This is a close-up image · the lesion involves the head or neck: 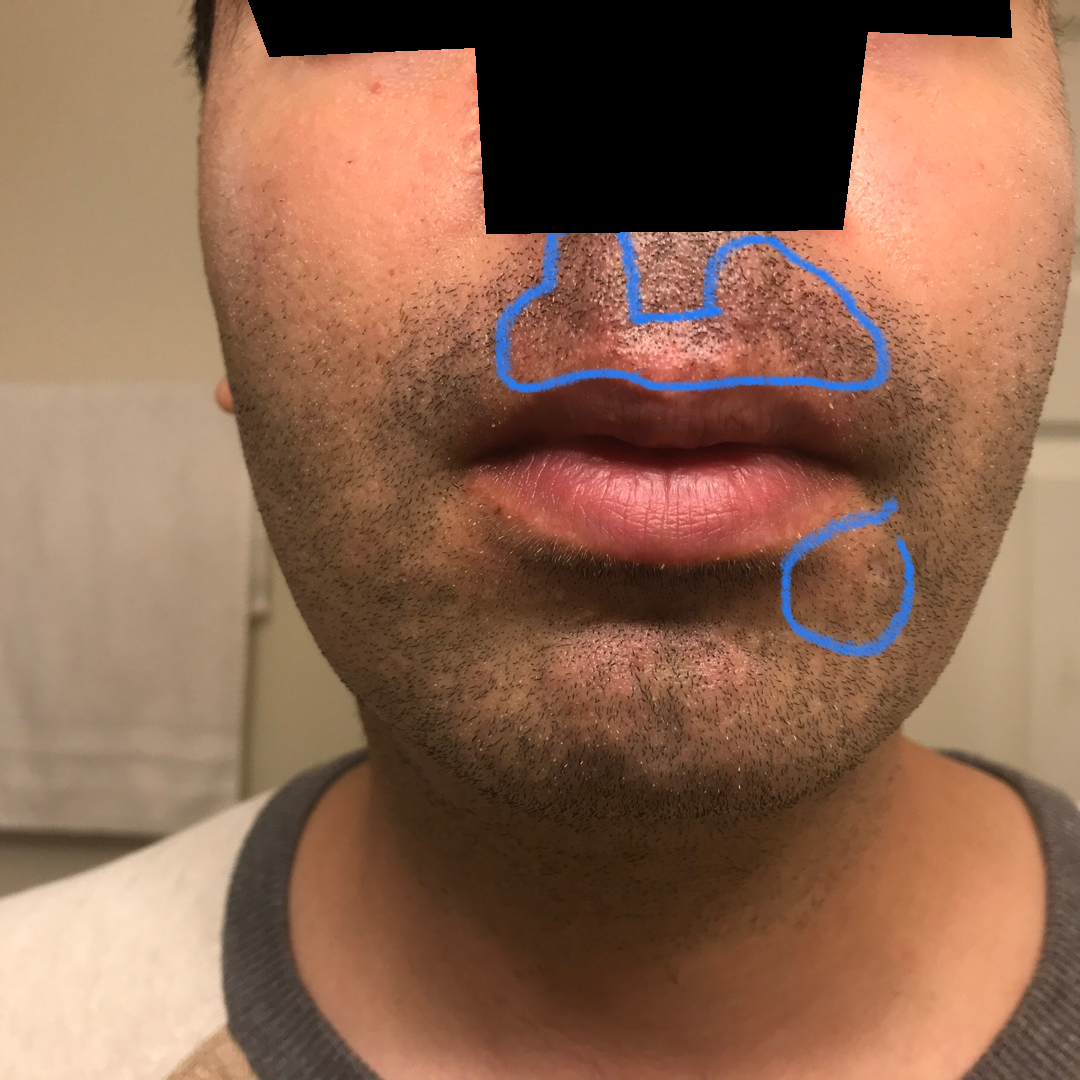assessment = not assessable
self-categorized as = a rash
present for = more than five years
constitutional symptoms = none reported
patient-reported symptoms = enlargement, burning and bothersome appearance
described texture = raised or bumpy and rough or flaky